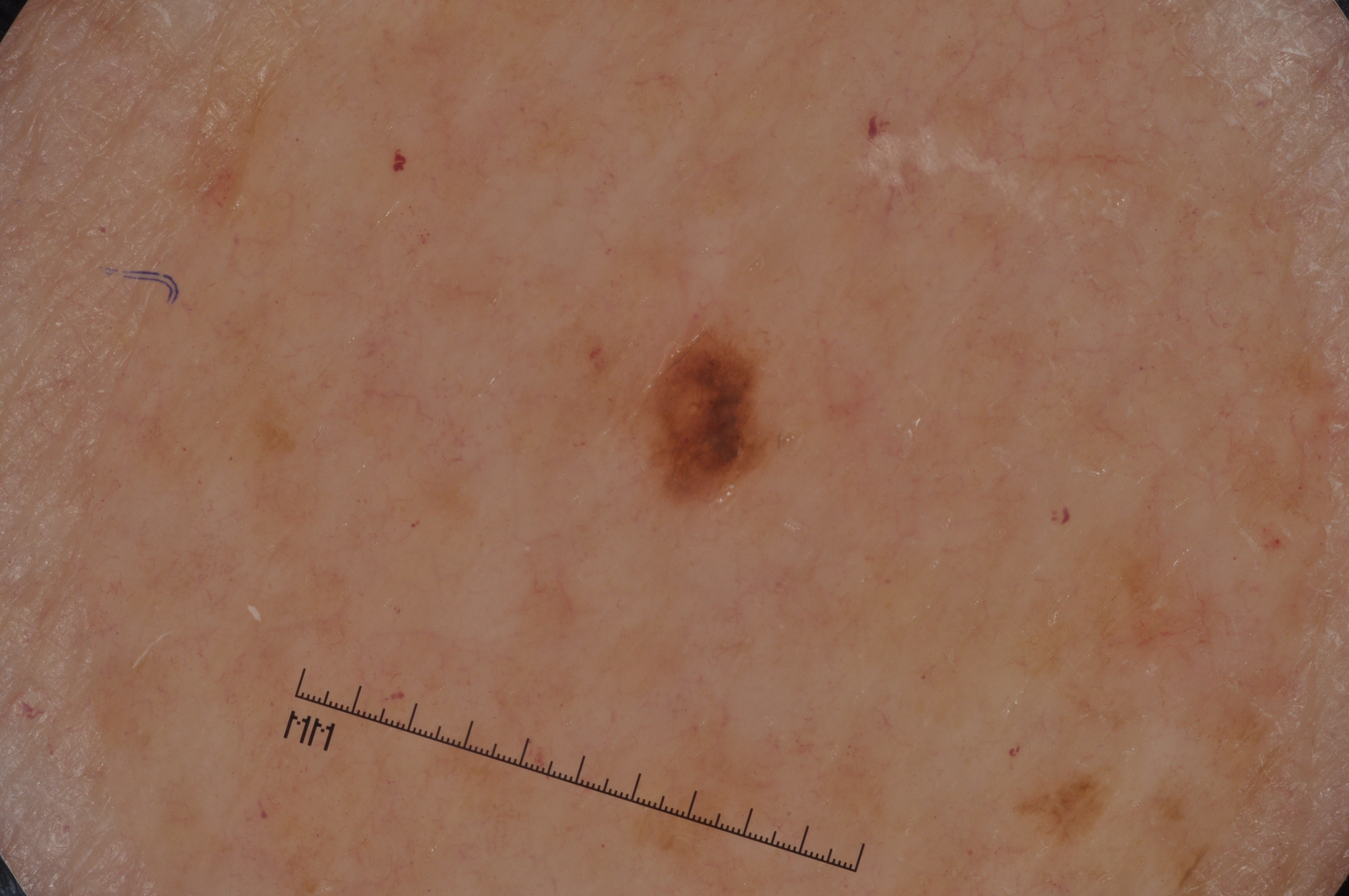Summary: A female patient, aged 63 to 67. This is a dermoscopic photograph of a skin lesion. With coordinates (x1, y1, x2, y2), the lesion spans 641, 327, 771, 505. A small lesion occupying a minor part of the field. Dermoscopy demonstrates pigment network. Impression: The clinical diagnosis was a melanocytic nevus.